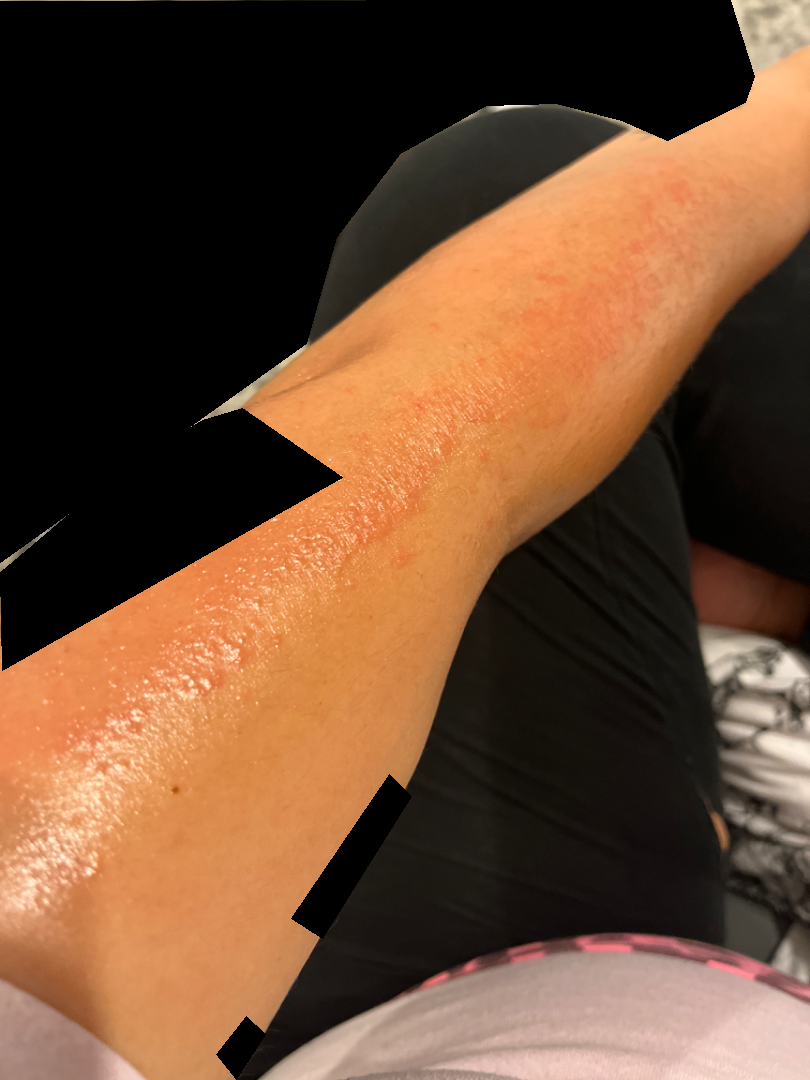This is a close-up image. Skin tone: Fitzpatrick skin type III. Acute dermatitis, NOS and Allergic Contact Dermatitis were considered with similar weight.